The lesion involves the back of the hand, leg, top or side of the foot, back of the torso, arm and head or neck · the photograph is a close-up of the affected area · the subject is 40–49, female.
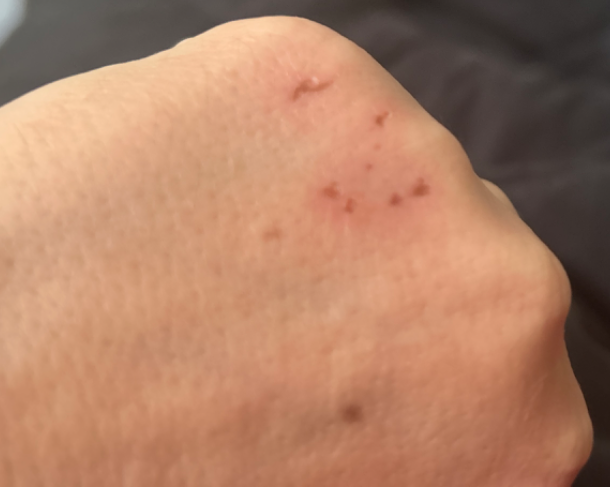Findings:
* assessment: indeterminate from the photograph
* present for: less than one week